Recorded as Fitzpatrick II. An overview clinical photograph of a skin lesion — 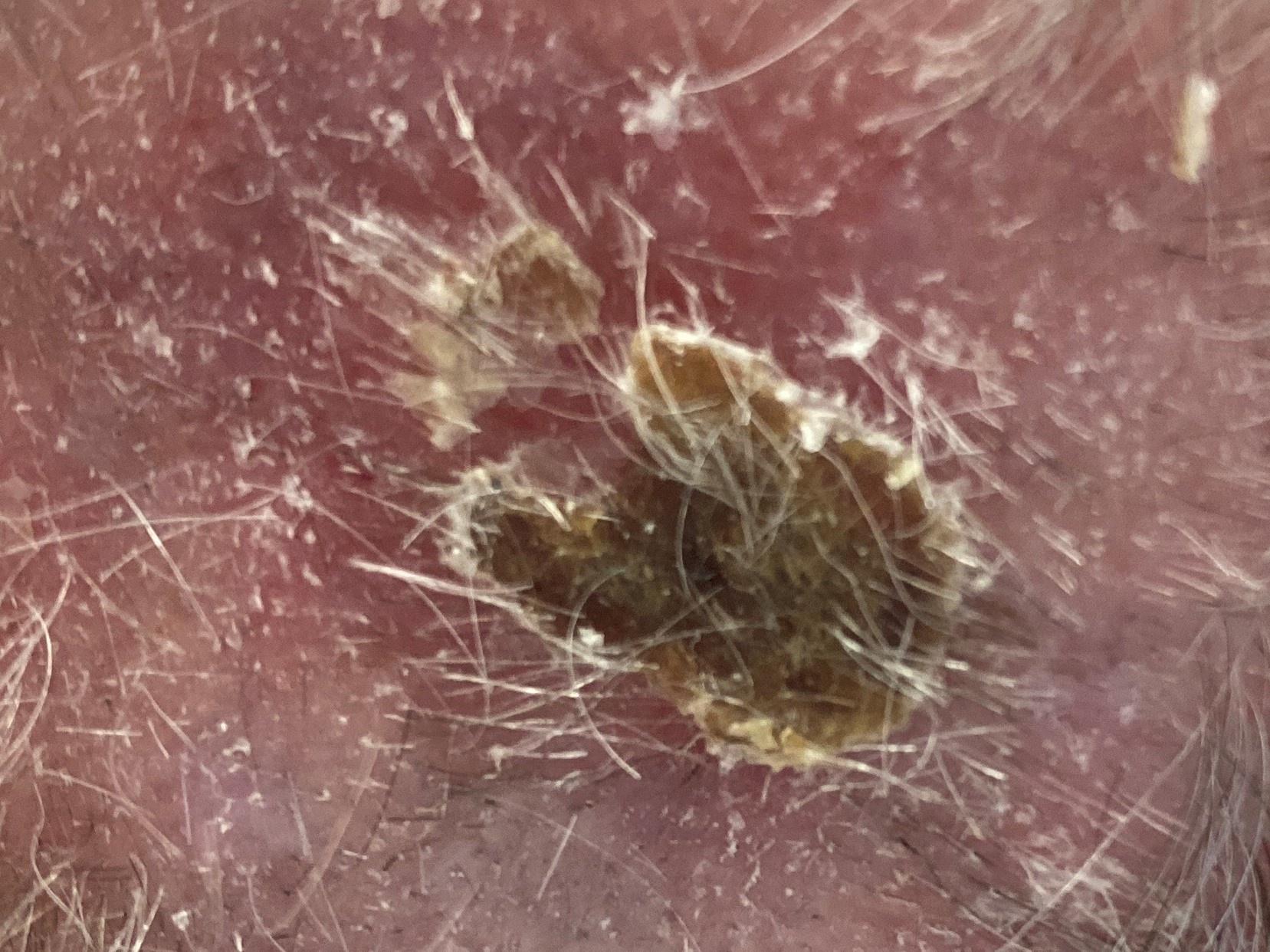diagnosis: Squamous cell carcinoma (biopsy-proven).